The condition has been present for one to four weeks · the subject is 40–49, female · the lesion is associated with pain and bothersome appearance · the photo was captured at an angle · texture is reported as rough or flaky and raised or bumpy · the affected area is the palm.
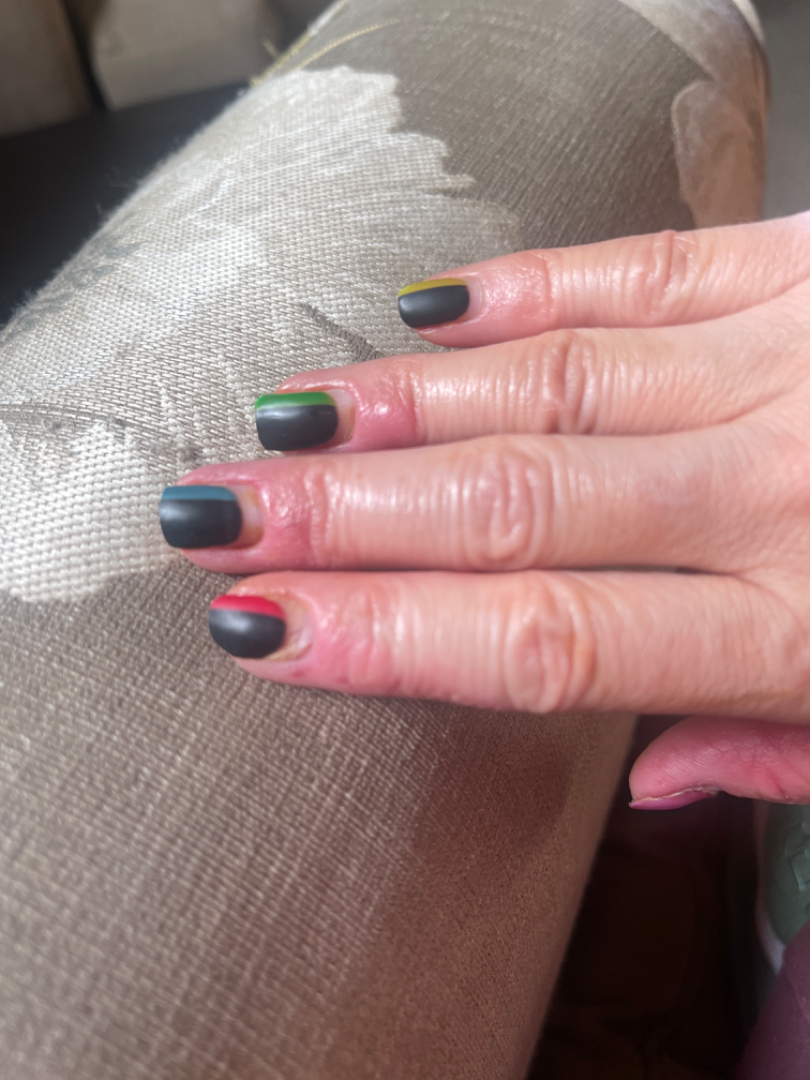The reviewing panel's impression was: Paronychia (weight 0.60); Eczema (weight 0.20); Allergic Contact Dermatitis (weight 0.20).